The lesion involves the back of the torso. A close-up photograph:
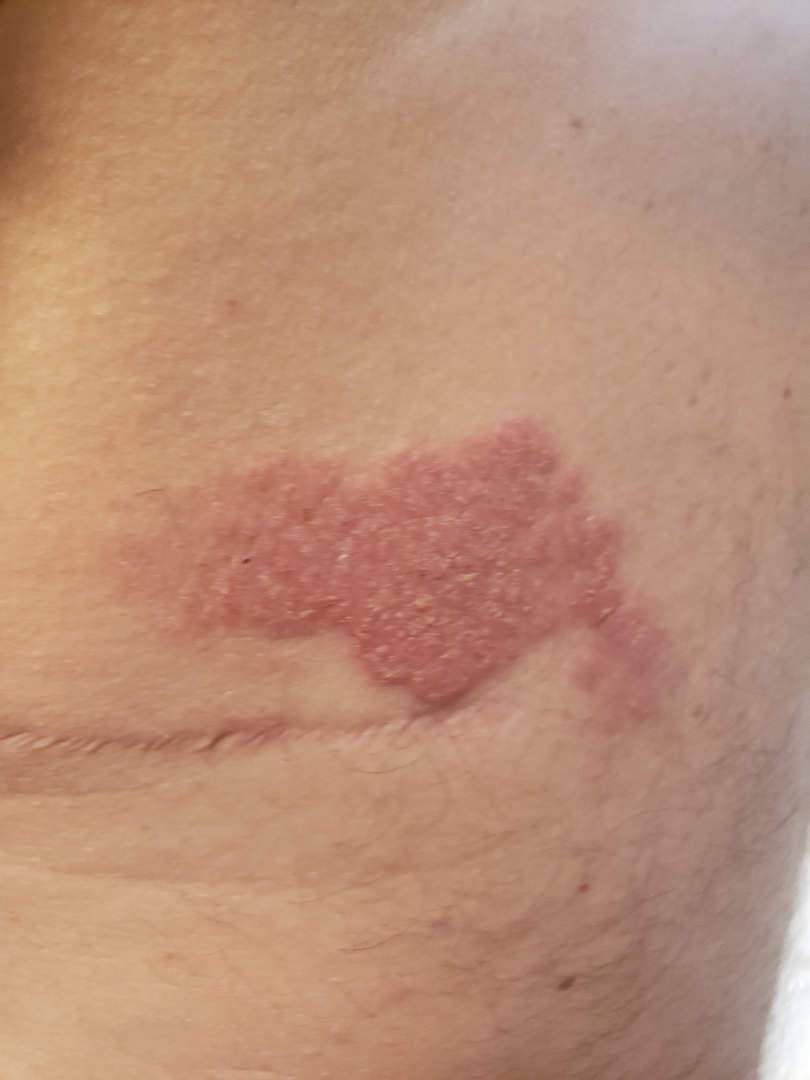| field | value |
|---|---|
| diagnostic considerations | most likely Psoriasis; possibly Eczema |